A dermoscopic image of a skin lesion:
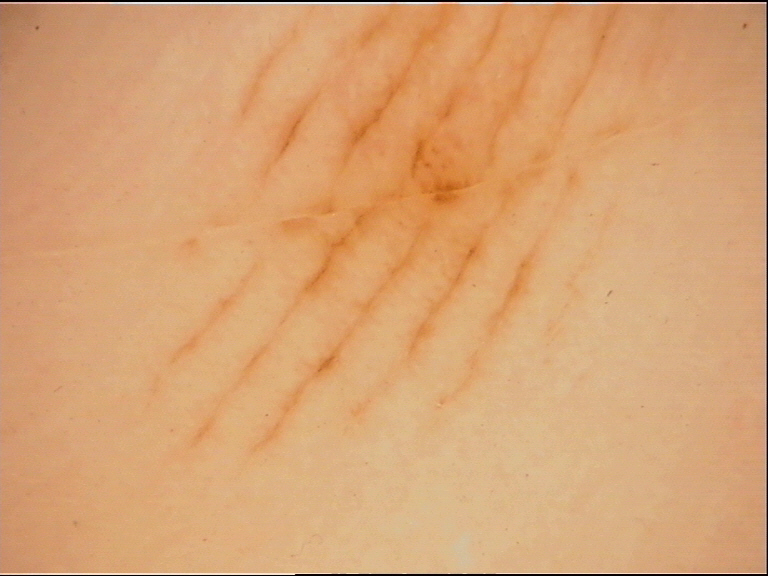Classified as an acral junctional nevus.